A male subject 51 years of age · a smartphone photograph of a skin lesion.
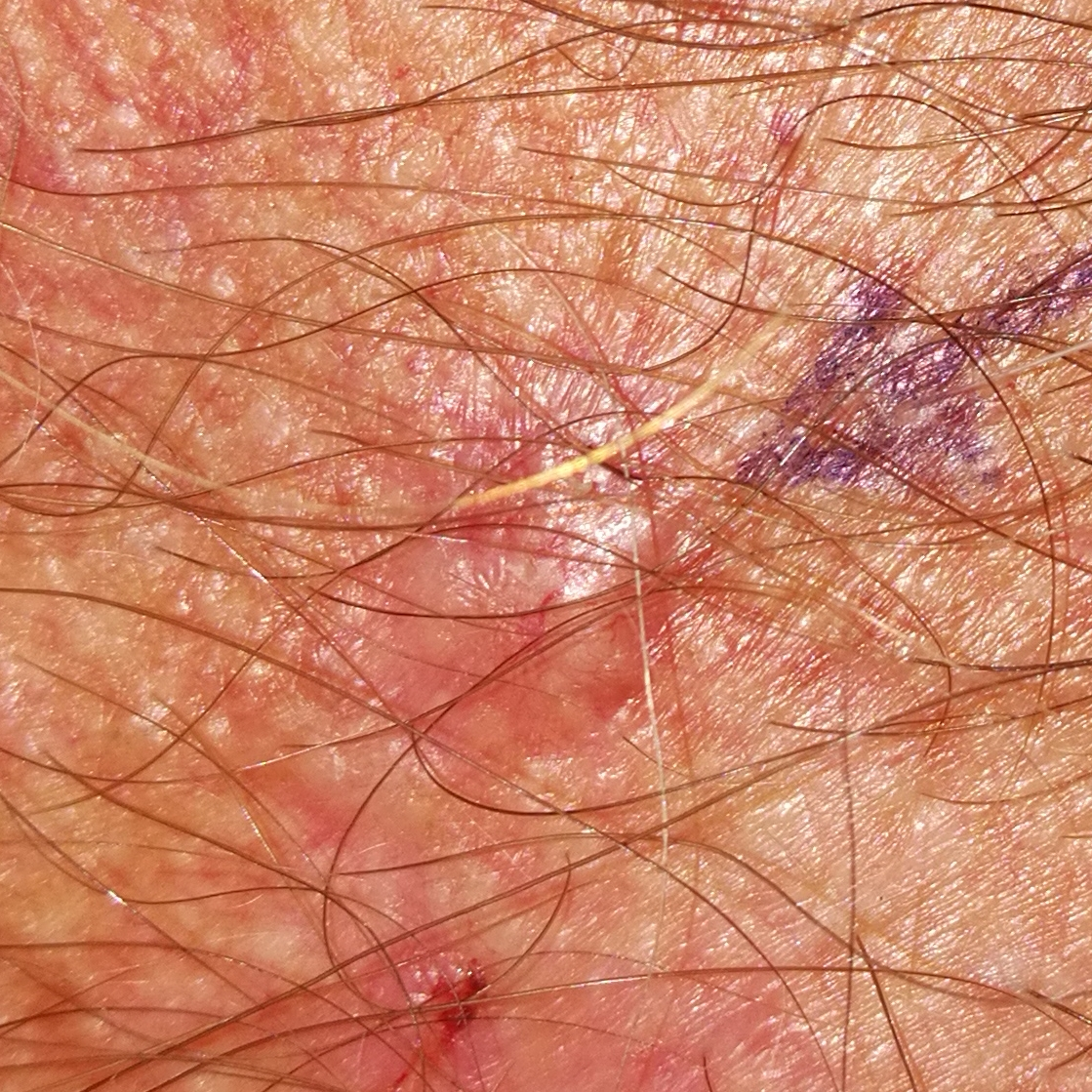Case summary: The lesion was found on the chest. Per patient report, the lesion hurts, itches, has bled, and is elevated. Conclusion: The biopsy diagnosis was a basal cell carcinoma.